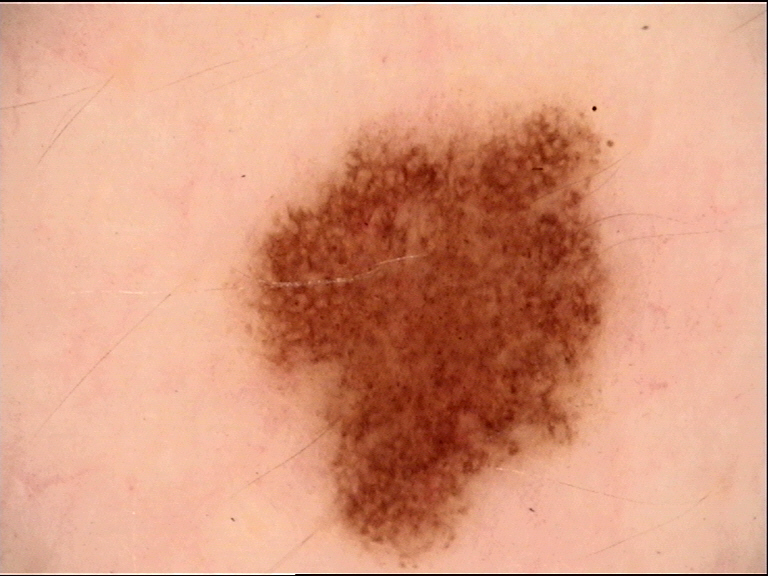A dermoscopic close-up of a skin lesion.
The diagnosis was a dysplastic junctional nevus.